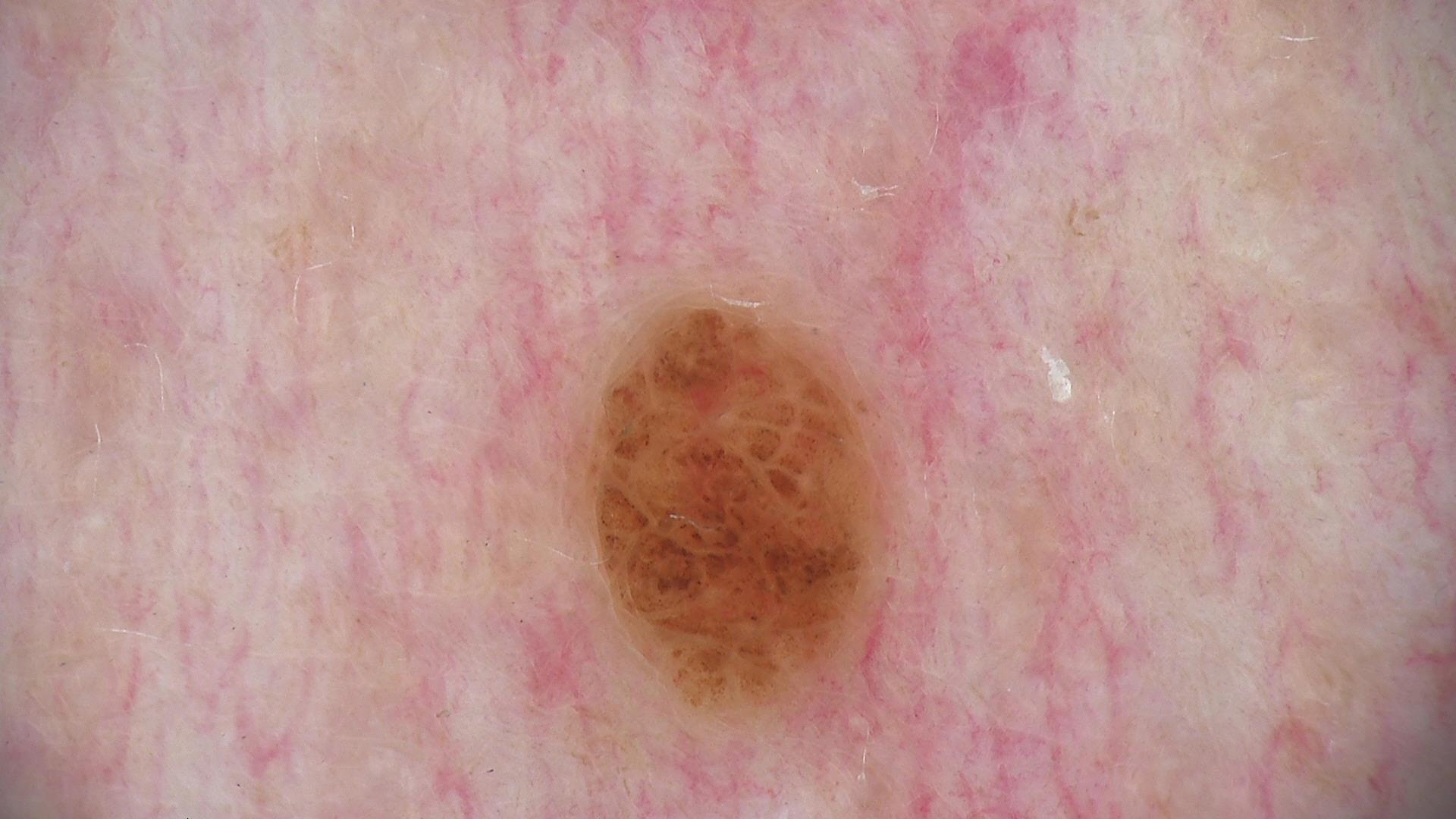Labeled as a compound nevus.